A dermoscopic image of a skin lesion.
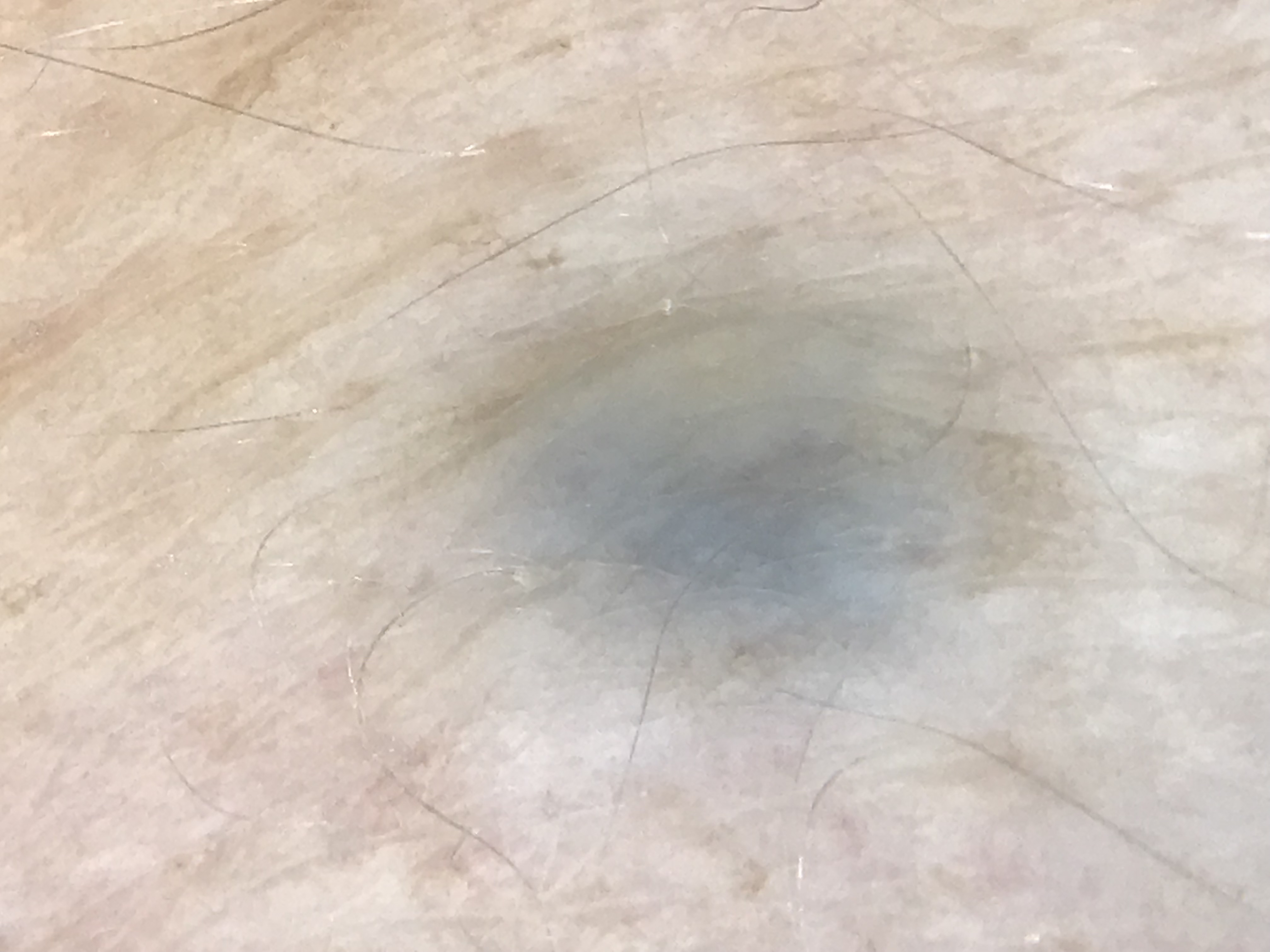class: blue nevus (expert consensus).